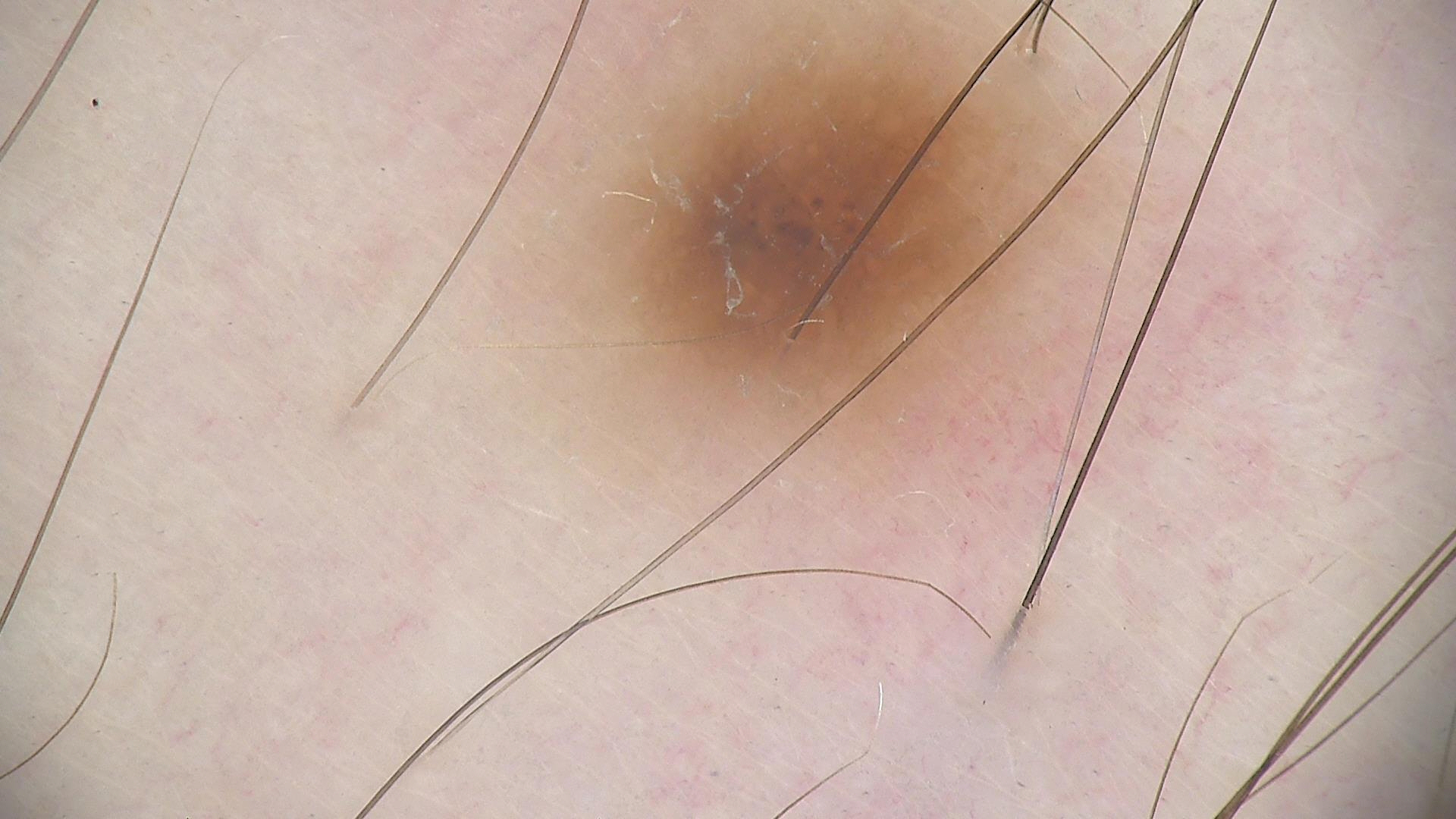A dermoscopic image of a skin lesion. The diagnostic label was a dysplastic junctional nevus.